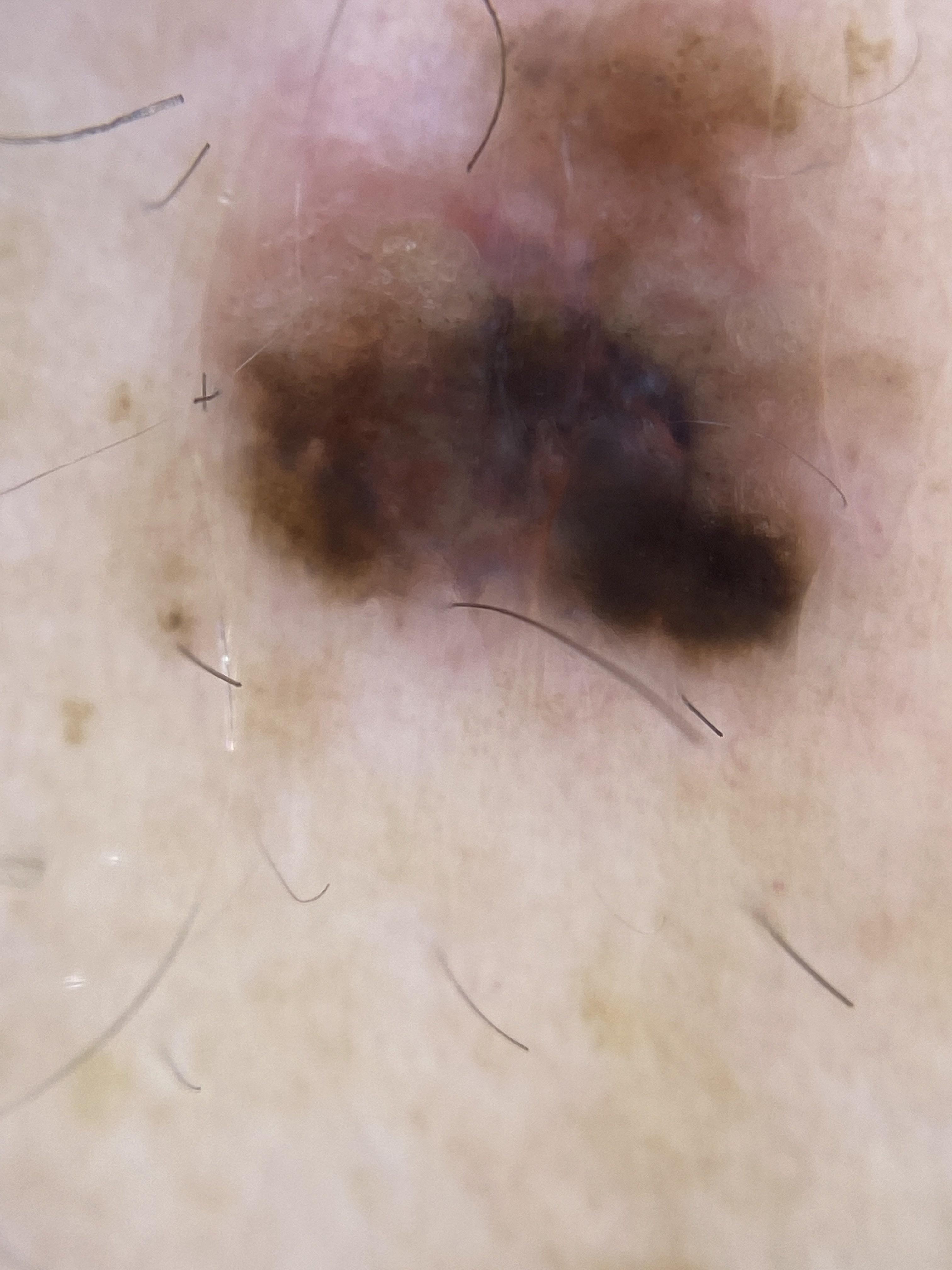A dermoscopic photograph of a skin lesion. The patient is Fitzpatrick phototype III. The lesion is located on the posterior trunk. Histopathology confirmed a nevus.